No relevant systemic symptoms. Located on the front of the torso. The photograph was taken at an angle. The condition has been present for about one day. No relevant lesion symptoms reported. The patient considered this skin that appeared healthy to them. Texture is reported as raised or bumpy.
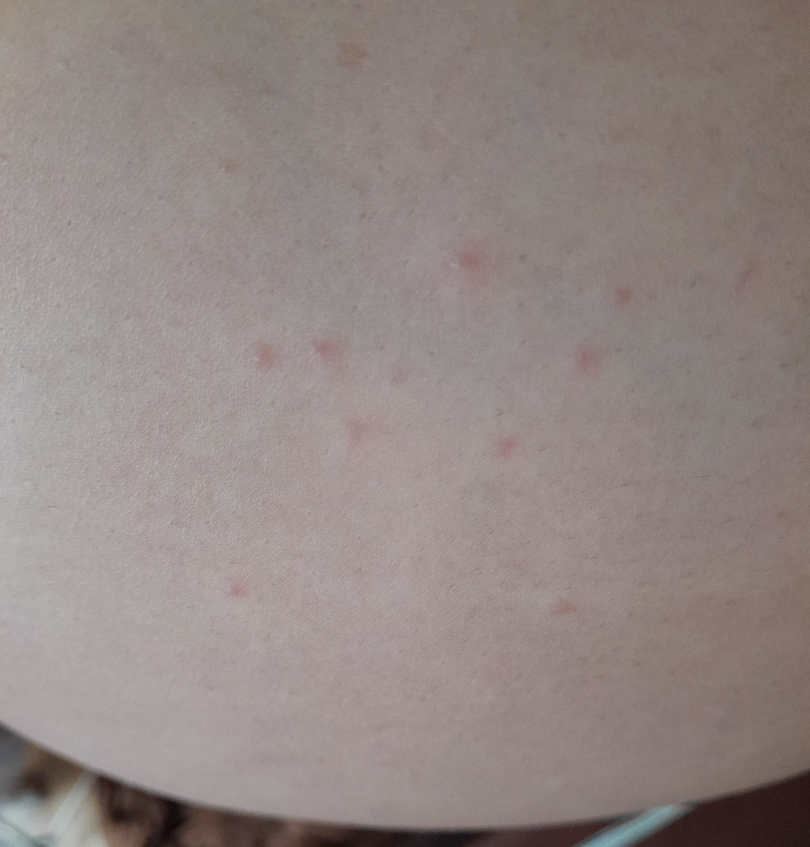{
  "assessment": "ungradable on photographic review"
}